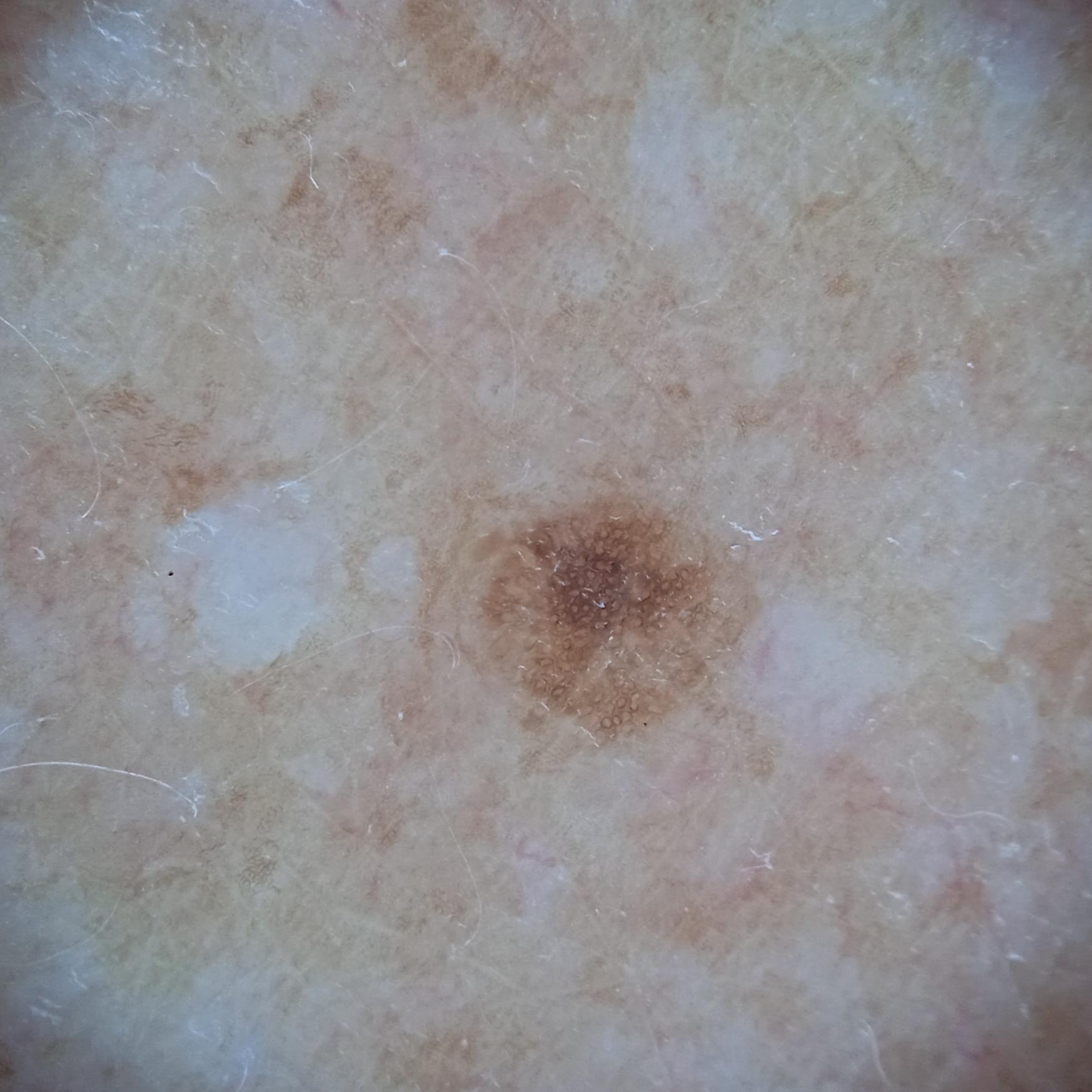nevus count: a moderate number of melanocytic nevi
sun reaction: skin tans without first burning
anatomic site: the back
lesion size: 2.7 mm
assessment: melanocytic nevus (dermatologist consensus)